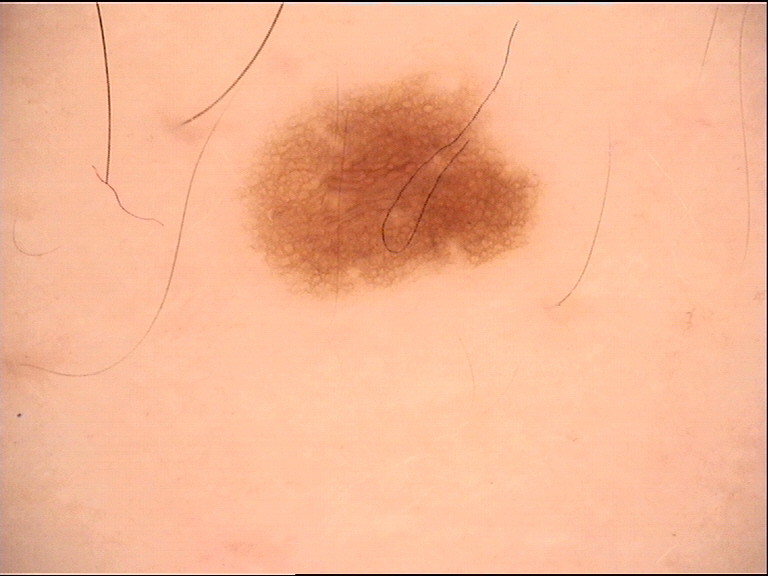label=dysplastic junctional nevus (expert consensus).